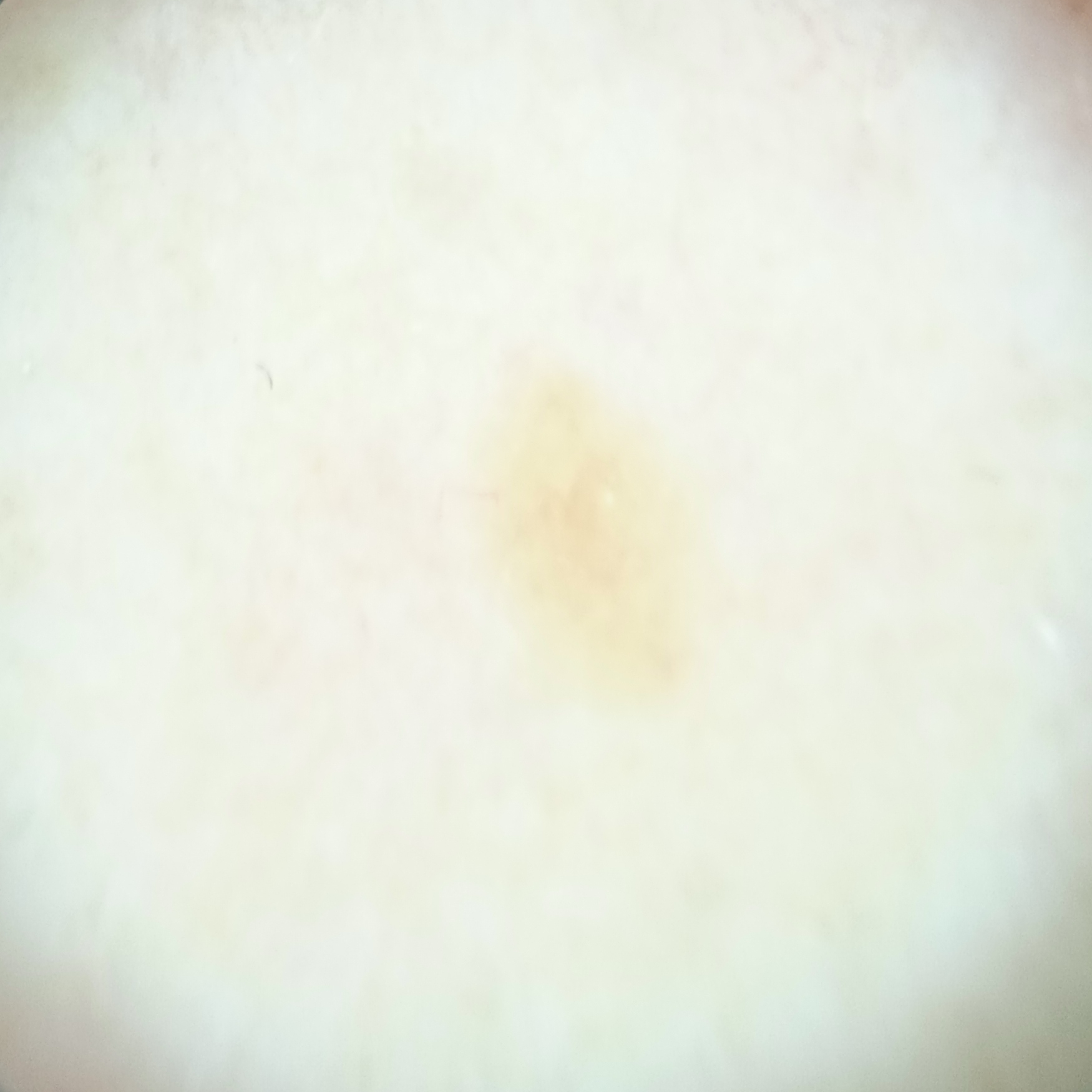Summary:
A dermoscopy image of a skin lesion. Imaged for a research study, with no referral diagnosis recorded. A female patient age 48. The lesion involves the back. Measuring roughly 3.8 mm.
Conclusion:
The dermatologists' assessment was a seborrheic keratosis.